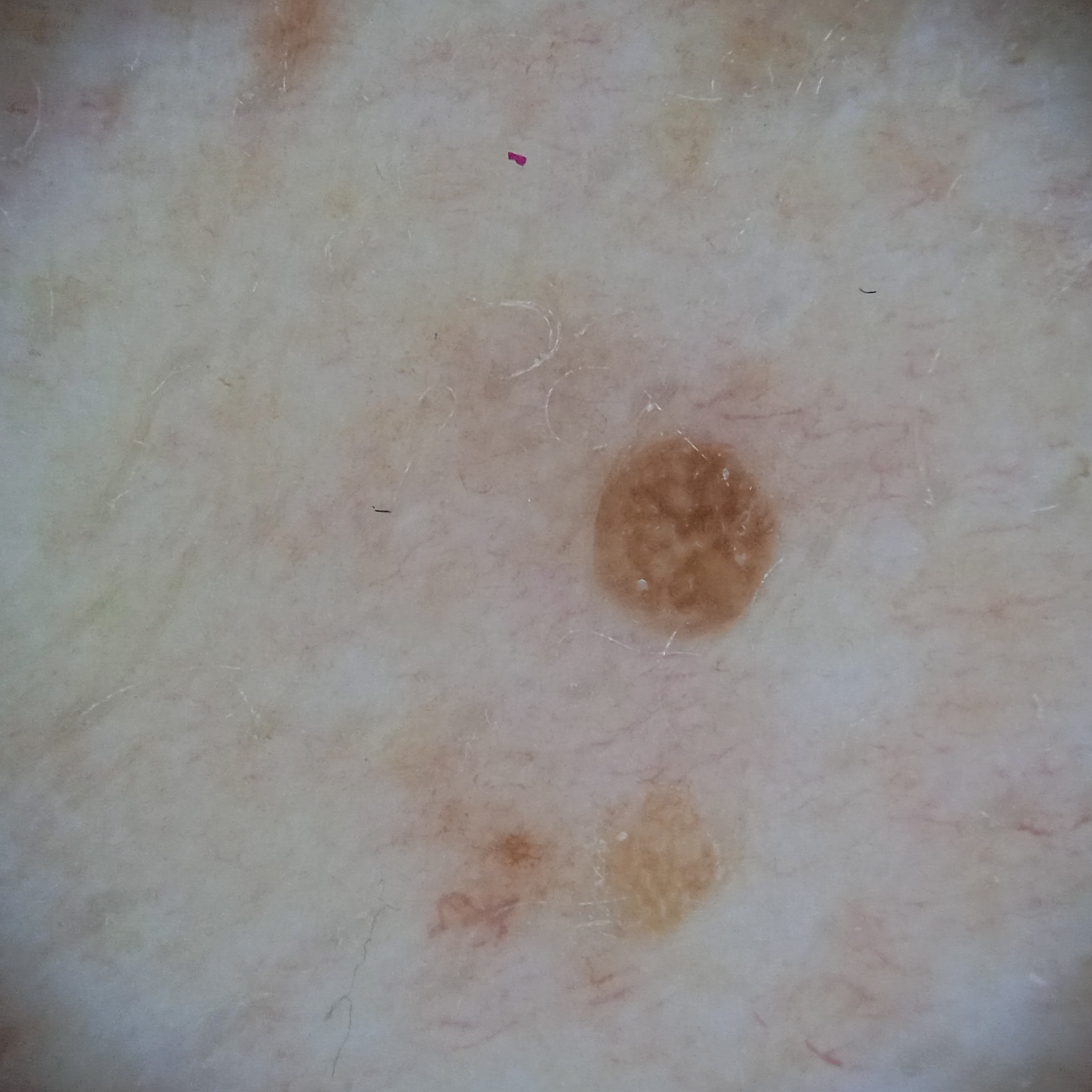Clinical context:
A skin lesion imaged with a dermatoscope. The patient says their skin reddens with sun exposure. Collected as part of a research study, without a referral diagnosis. A female patient 59 years old. On a questionnaire the patient reported no immunosuppression and no sunbed use. The patient describes having a moderate number of moles. Located on the torso. Measuring roughly 2.2 mm.
Assessment:
Reviewed by four dermatologists, the consensus diagnosis was a seborrheic keratosis; the four reviewers were unanimous; the reviewers were moderately confident; an alternative consideration was a melanocytic nevus.